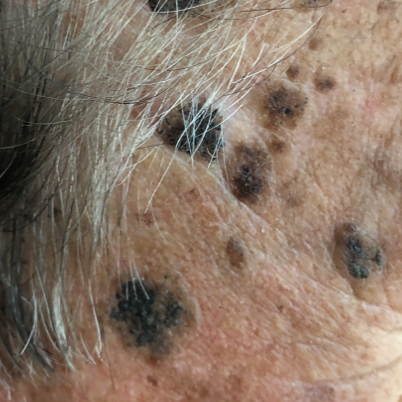Case summary: A subject in their 70s. A clinical photograph showing a skin lesion. The lesion involves the face. The patient reports that the lesion is elevated and has grown, but has not bled and does not hurt. Conclusion: The consensus clinical diagnosis was a seborrheic keratosis.